The contributor is male · an image taken at a distance · the affected area is the top or side of the foot and leg — 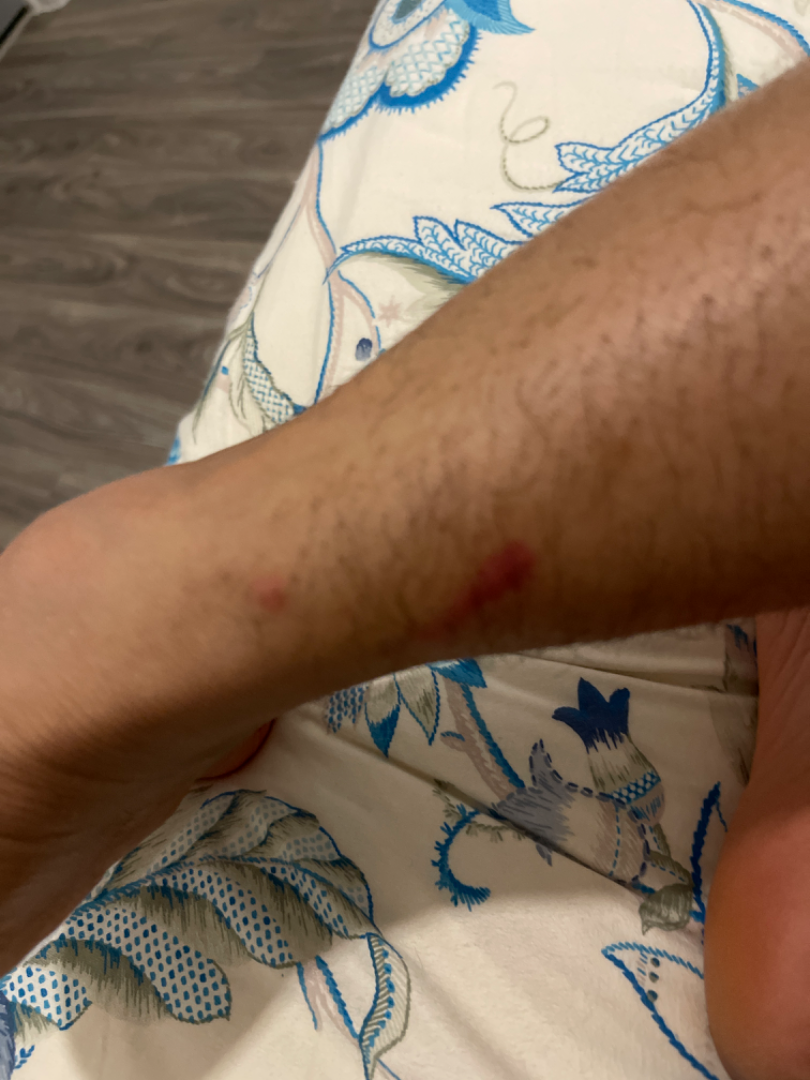Findings:
The reviewing dermatologists' impression was: the differential includes Insect Bite and Urticaria, with no clear leading consideration; possibly Allergic Contact Dermatitis.